This is a close-up image, the leg is involved:
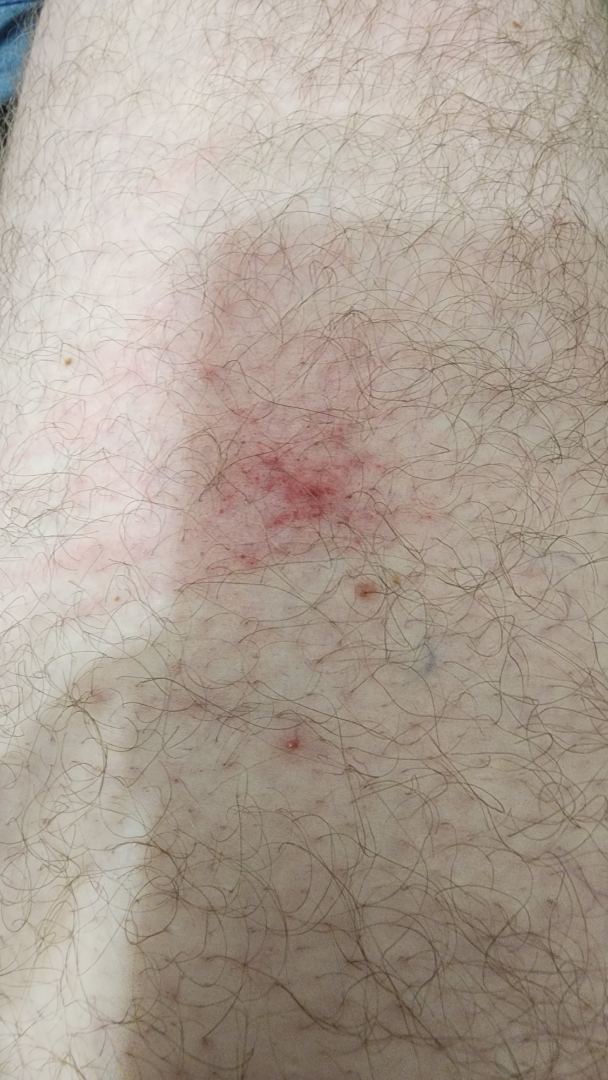assessment: indeterminate from the photograph; present for: less than one week; self-categorized as: a rash; symptoms: bleeding, itching and enlargement; texture: fluid-filled and raised or bumpy.